The photo was captured at a distance — 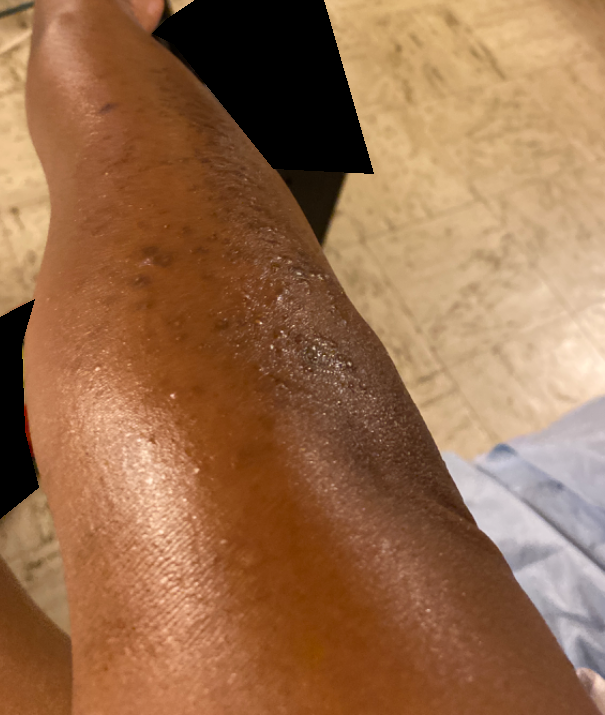The case was indeterminate on photographic review.
Reported duration is more than one year.